A dermoscopic image of a skin lesion — 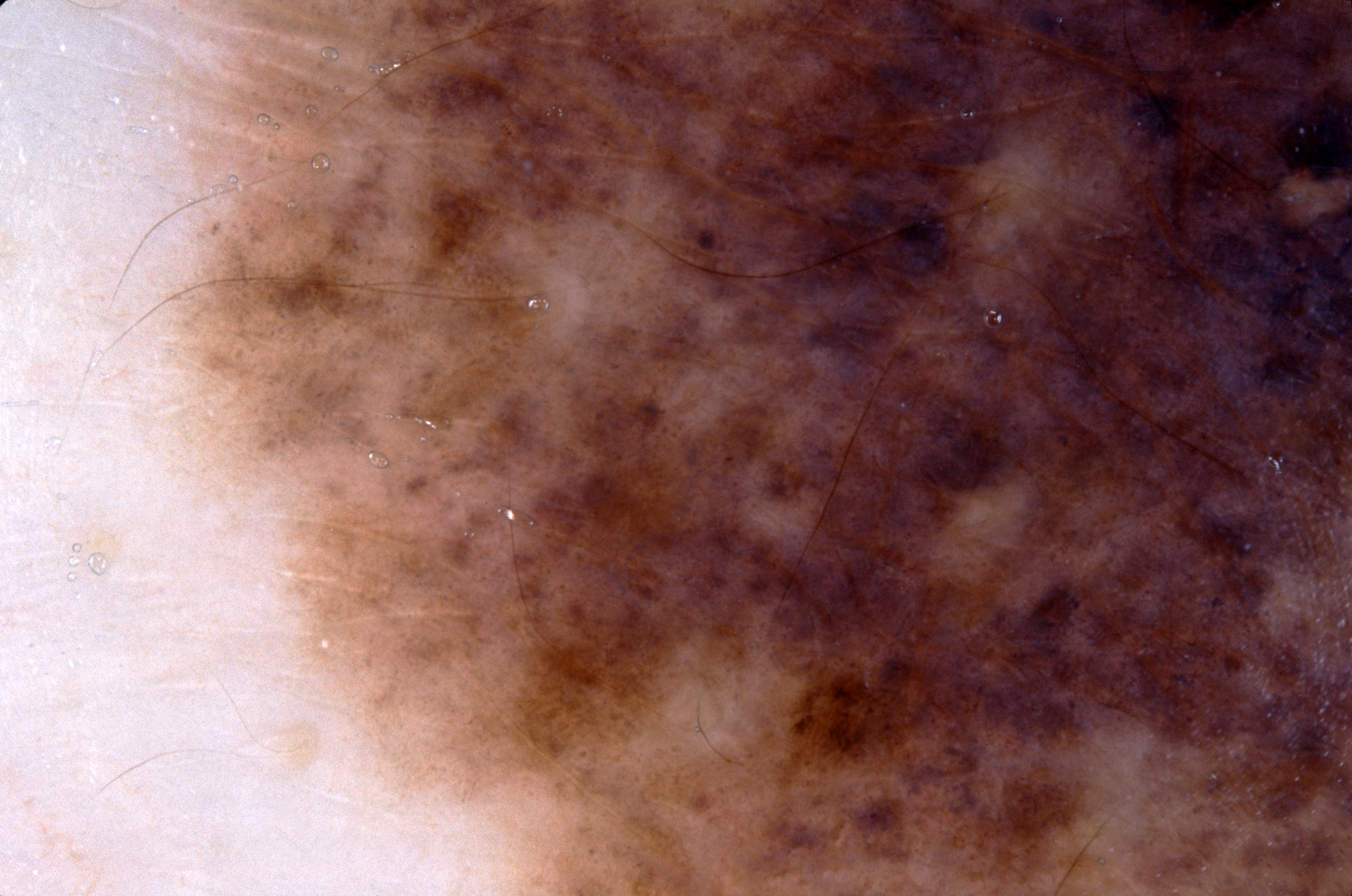Notes:
• lesion location · [158, 0, 1351, 895]
• dermoscopic features not present · streaks, pigment network, milia-like cysts, and negative network
• impression · a melanocytic nevus, a benign skin lesion